A dermoscopy image of a single skin lesion. A female patient aged 73 to 77 — 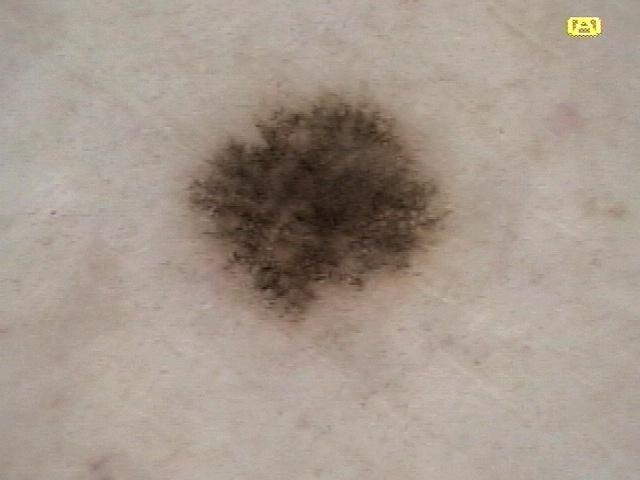Image and clinical context: Located on a lower extremity. Conclusion: Histopathologically confirmed as a nevus.